The patient is FST II; a male patient aged 76; a smartphone photograph of a skin lesion:
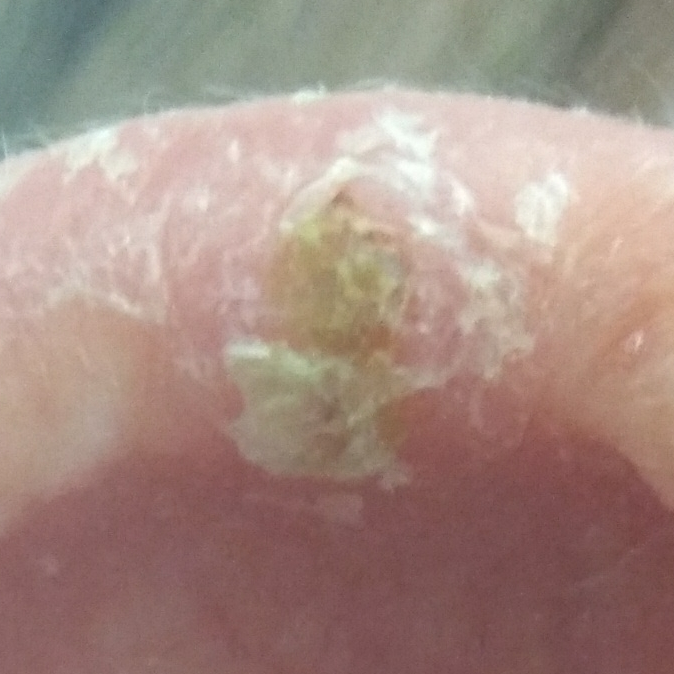<record>
<lesion_location>an ear</lesion_location>
<lesion_size>
<diameter_1_mm>5.0</diameter_1_mm>
<diameter_2_mm>3.0</diameter_2_mm>
</lesion_size>
<symptoms>
<present>itching</present>
<absent>bleeding, elevation</absent>
</symptoms>
<diagnosis>
<name>actinic keratosis</name>
<code>ACK</code>
<malignancy>indeterminate</malignancy>
<confirmation>histopathology</confirmation>
</diagnosis>
</record>